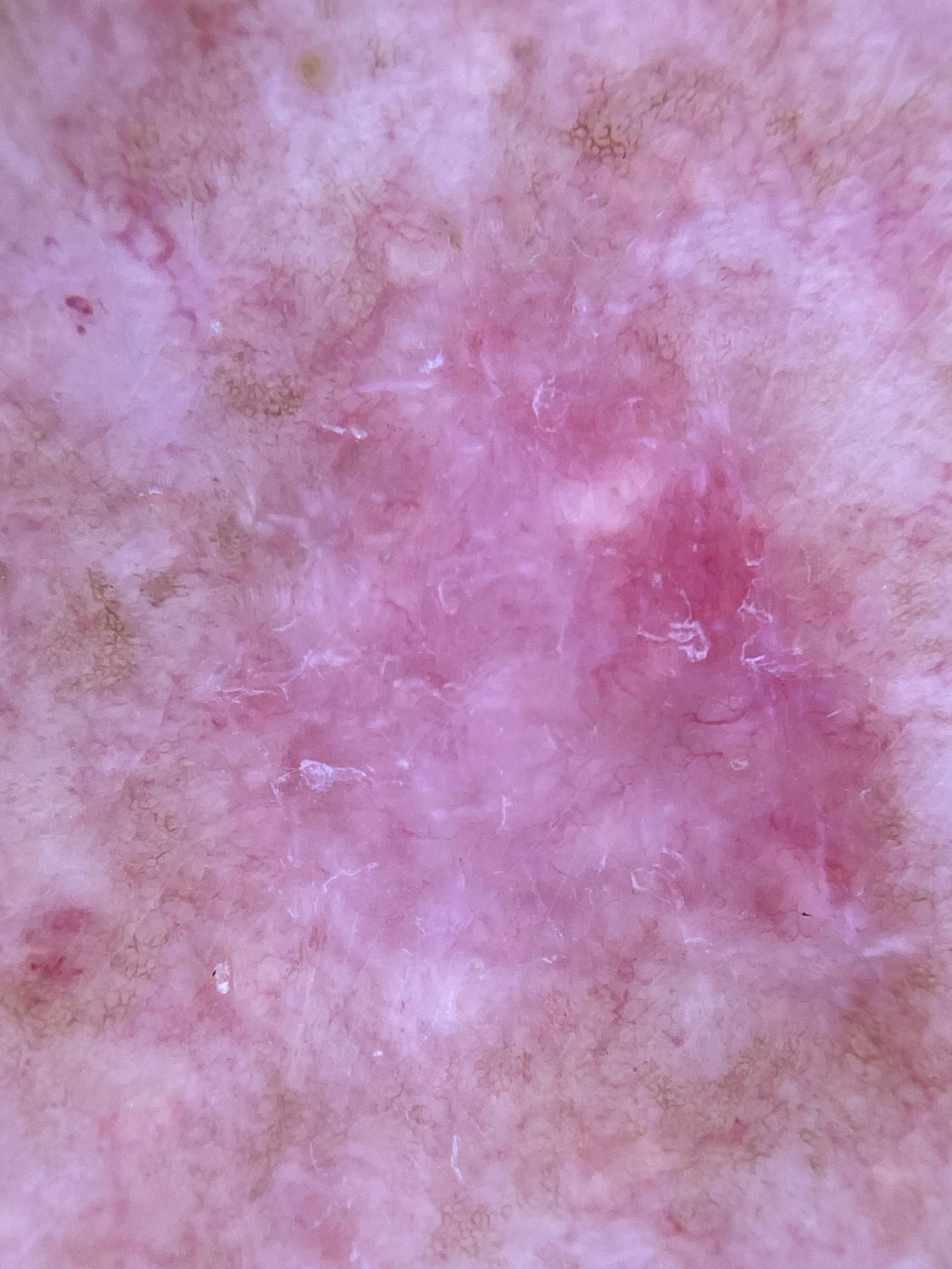| key | value |
|---|---|
| melanoma history | a previous melanoma |
| image | dermoscopy |
| site | the trunk |
| diagnosis | Basal cell carcinoma (biopsy-proven) |